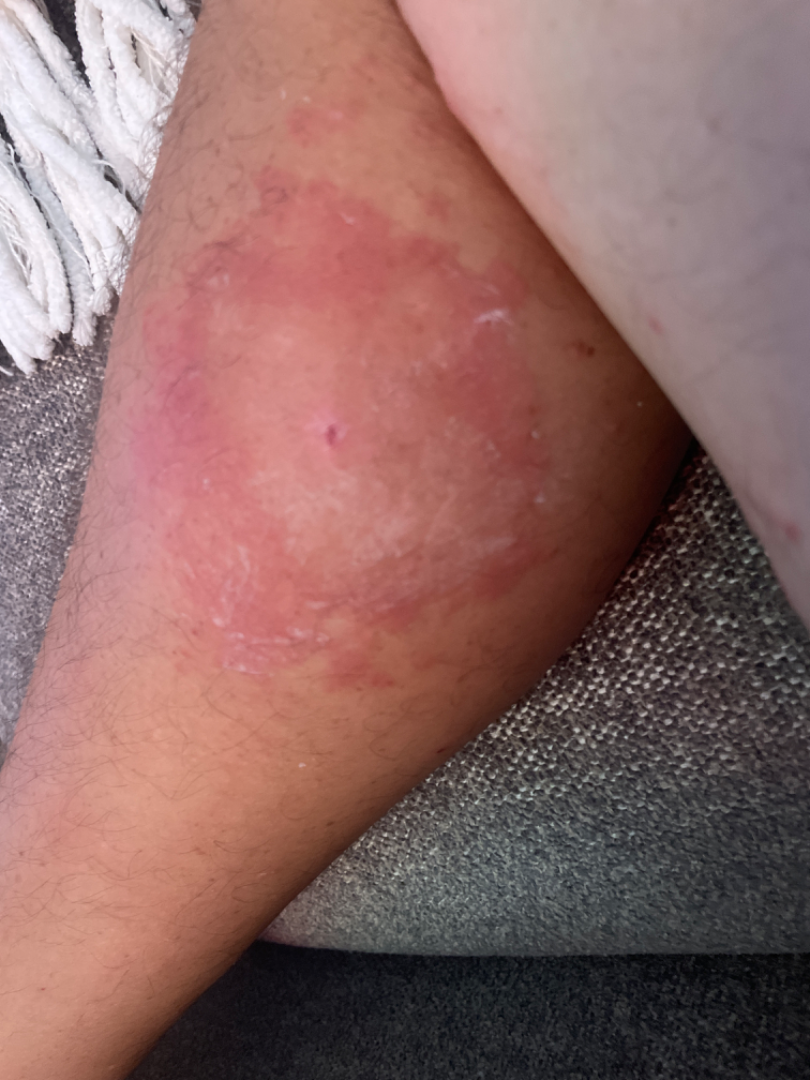• self-categorized as: a rash
• location: leg
• lesion symptoms: enlargement and itching
• contributor: male
• duration: one to four weeks
• described texture: raised or bumpy
• shot type: close-up
• constitutional symptoms: none reported
• clinical impression: most consistent with Insect Bite; also on the differential is Cellulitis; less probable is Abscess; a remote consideration is Fungal dermatosis; less likely is Cutaneous lyme disease